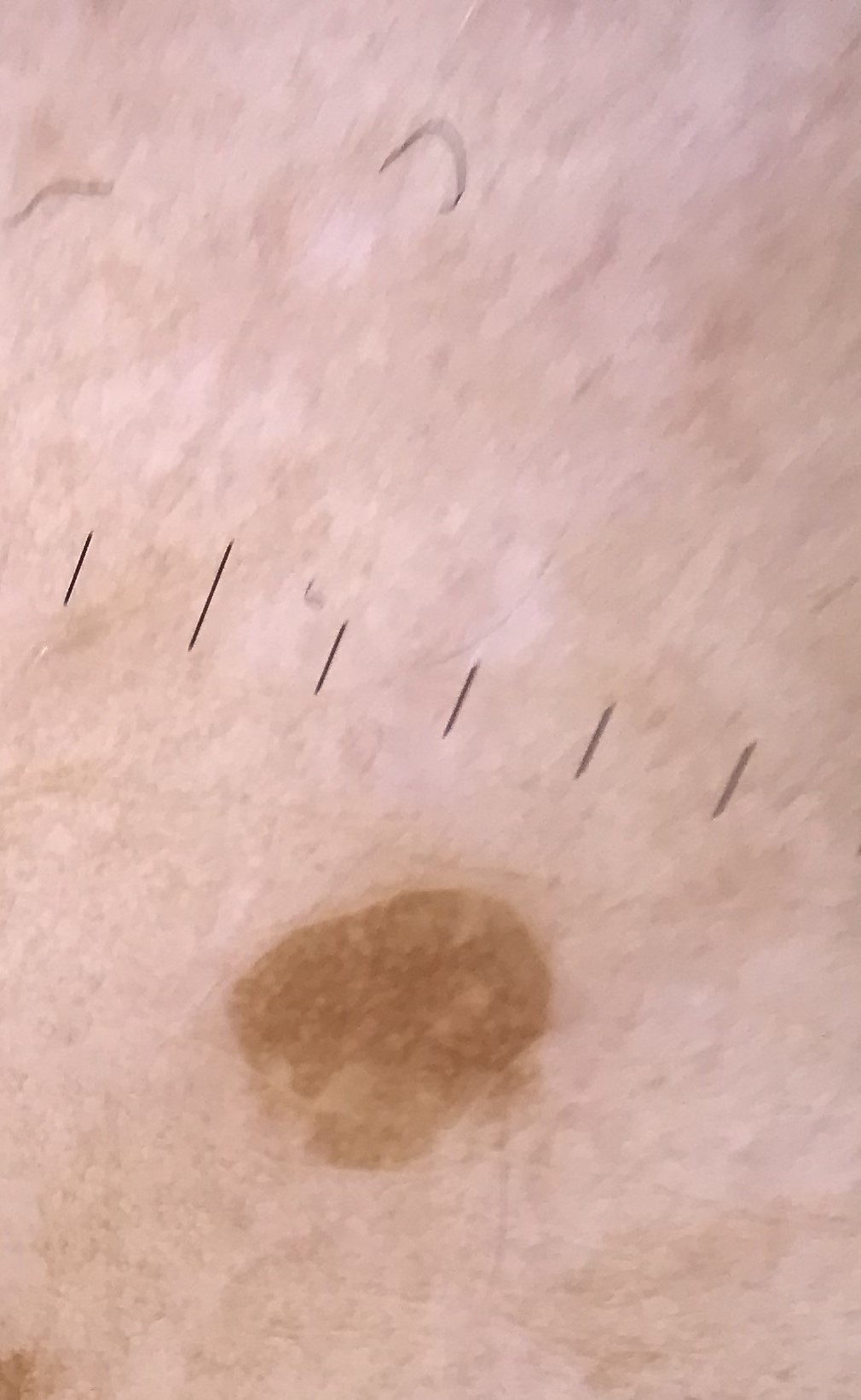A dermoscopy image of a single skin lesion. This is a keratinocytic lesion. Labeled as a benign lesion — a seborrheic keratosis.